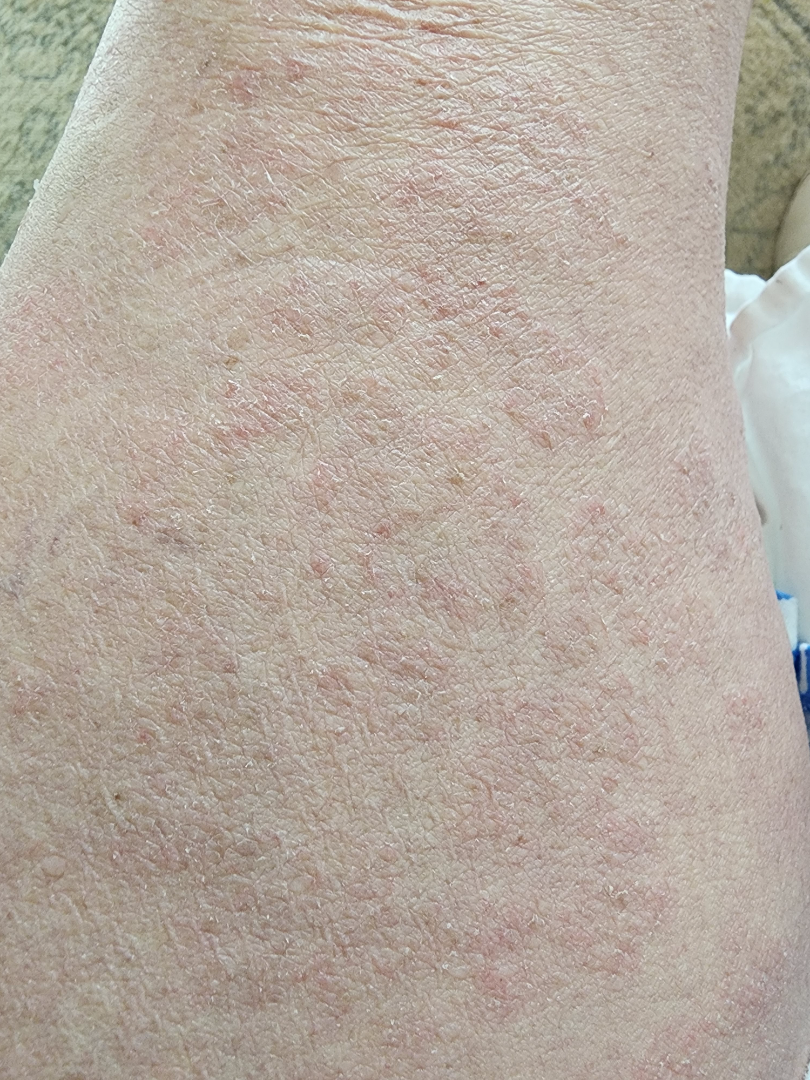On photographic review: consistent with Xerosis.